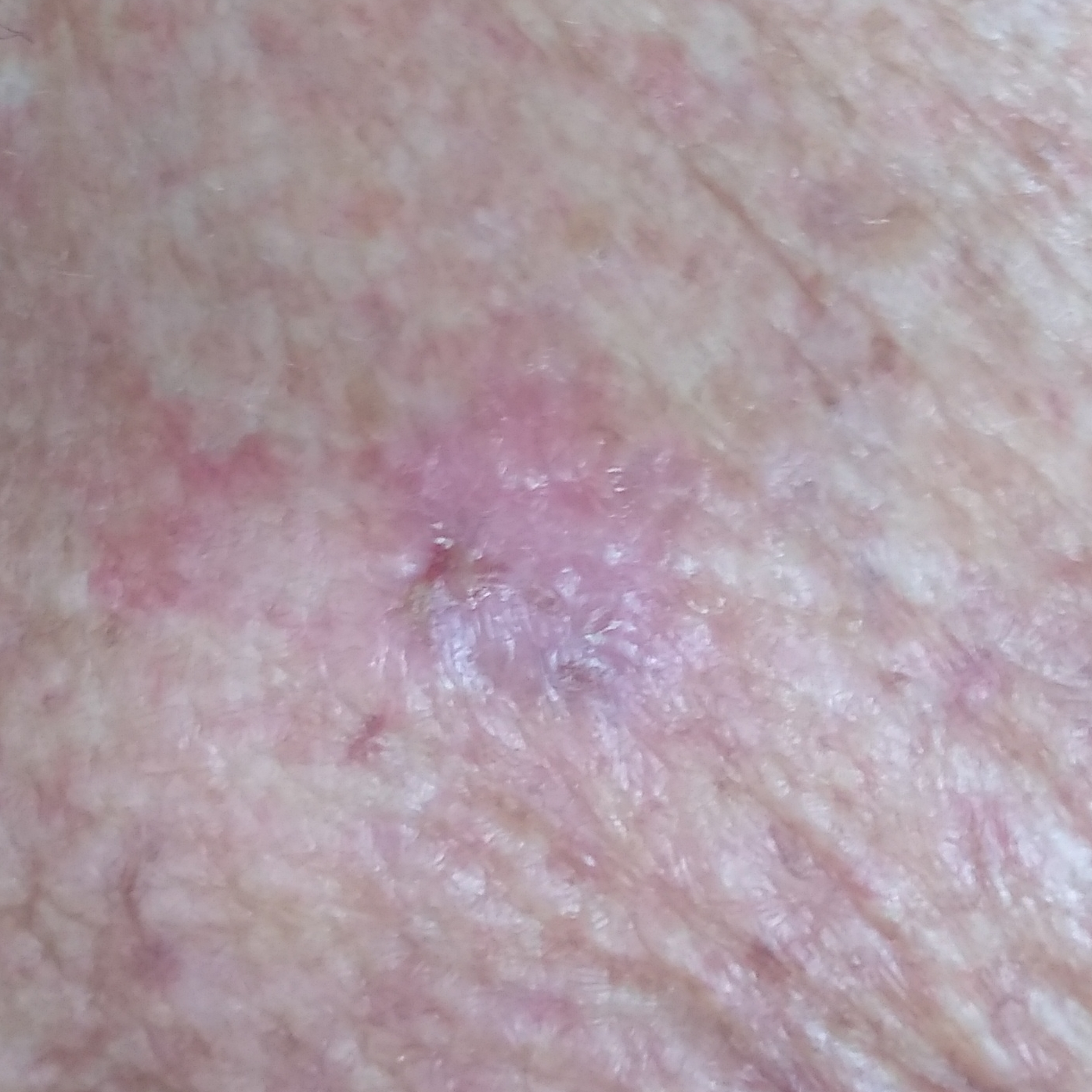{
  "patient": {
    "age": 53,
    "gender": "female"
  },
  "risk_factors": {
    "positive": [
      "pesticide exposure",
      "prior skin cancer (patient or family)"
    ]
  },
  "skin_type": "III",
  "symptoms": {
    "present": [
      "elevation",
      "itching"
    ]
  },
  "diagnosis": {
    "name": "basal cell carcinoma",
    "code": "BCC",
    "malignancy": "malignant",
    "confirmation": "histopathology"
  }
}